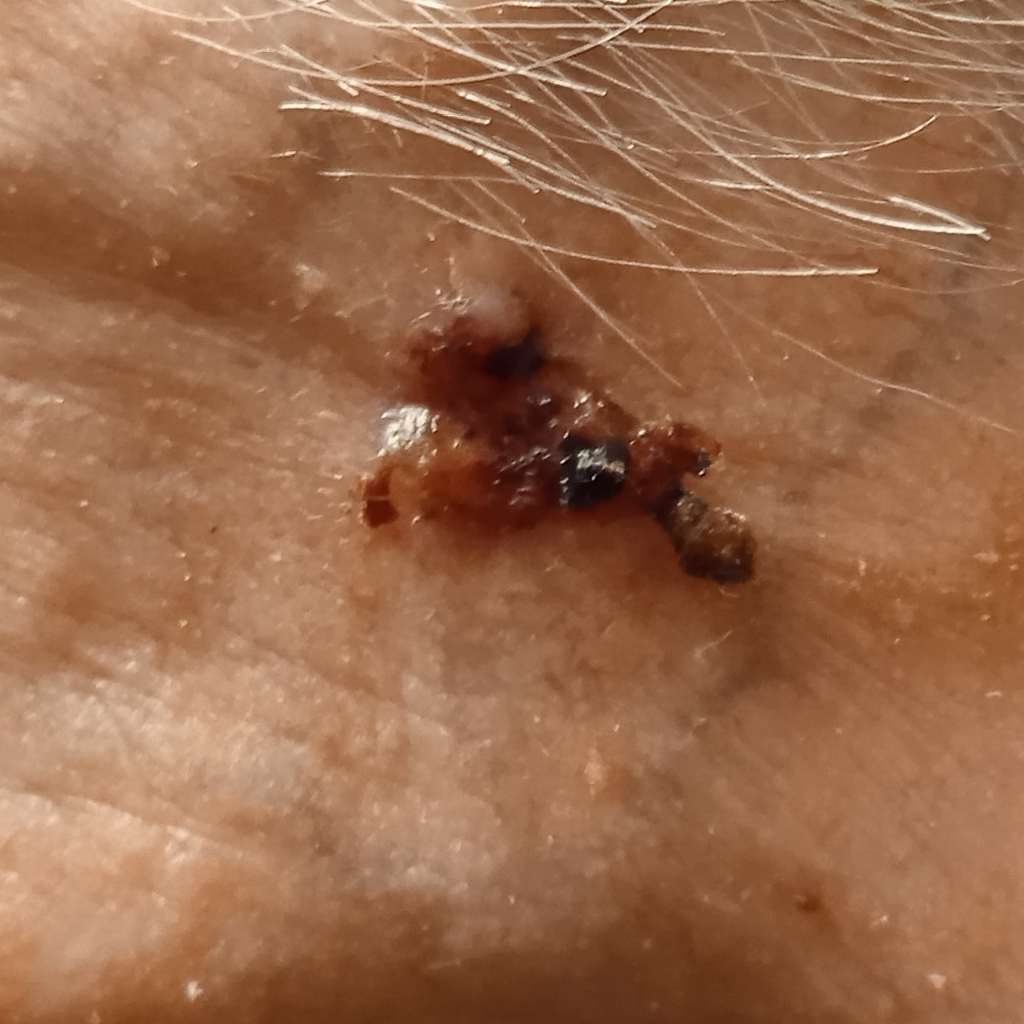A macroscopic clinical photograph of a skin lesion. Referred for assessment of suspected basal cell carcinoma. A male subject 89 years of age. Measuring roughly 14.9 mm. On biopsy, the diagnosis was a basal cell carcinoma, following excision, with a measured tumor thickness of 2 mm.